A dermoscopic view of a skin lesion: 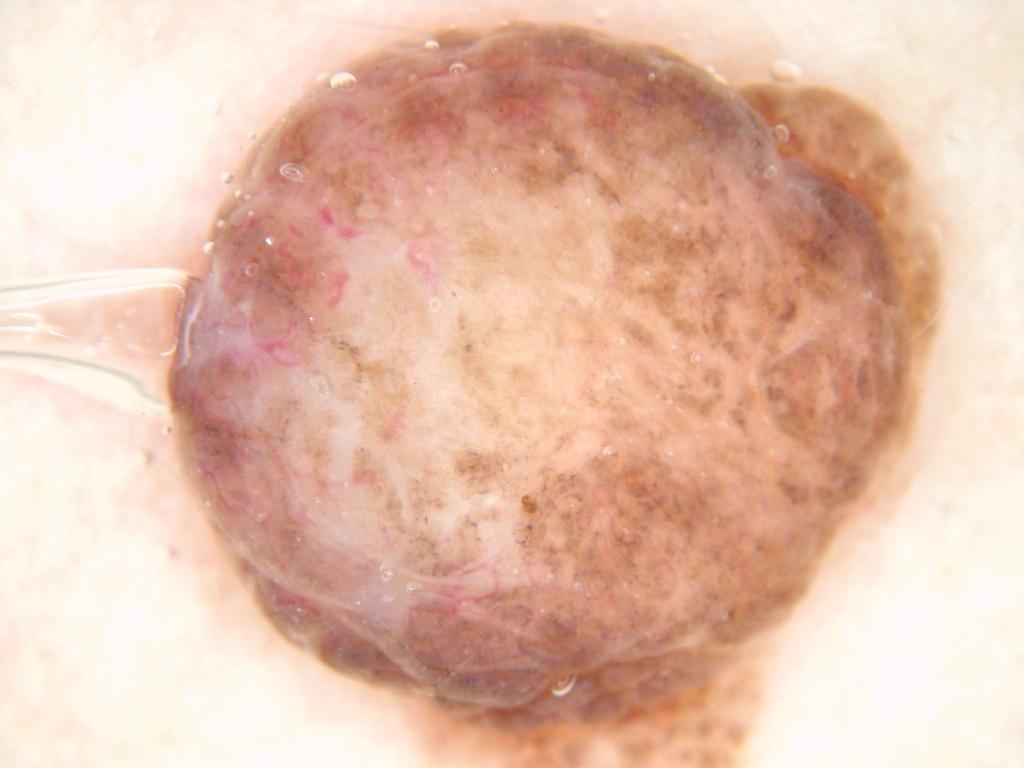Case summary: The lesion is located at [155, 9, 951, 766]. Conclusion: The lesion was assessed as a benign lesion.